A female subject in their 50s. A clinical photograph showing a skin lesion. History notes pesticide exposure and prior skin cancer (patient or family): 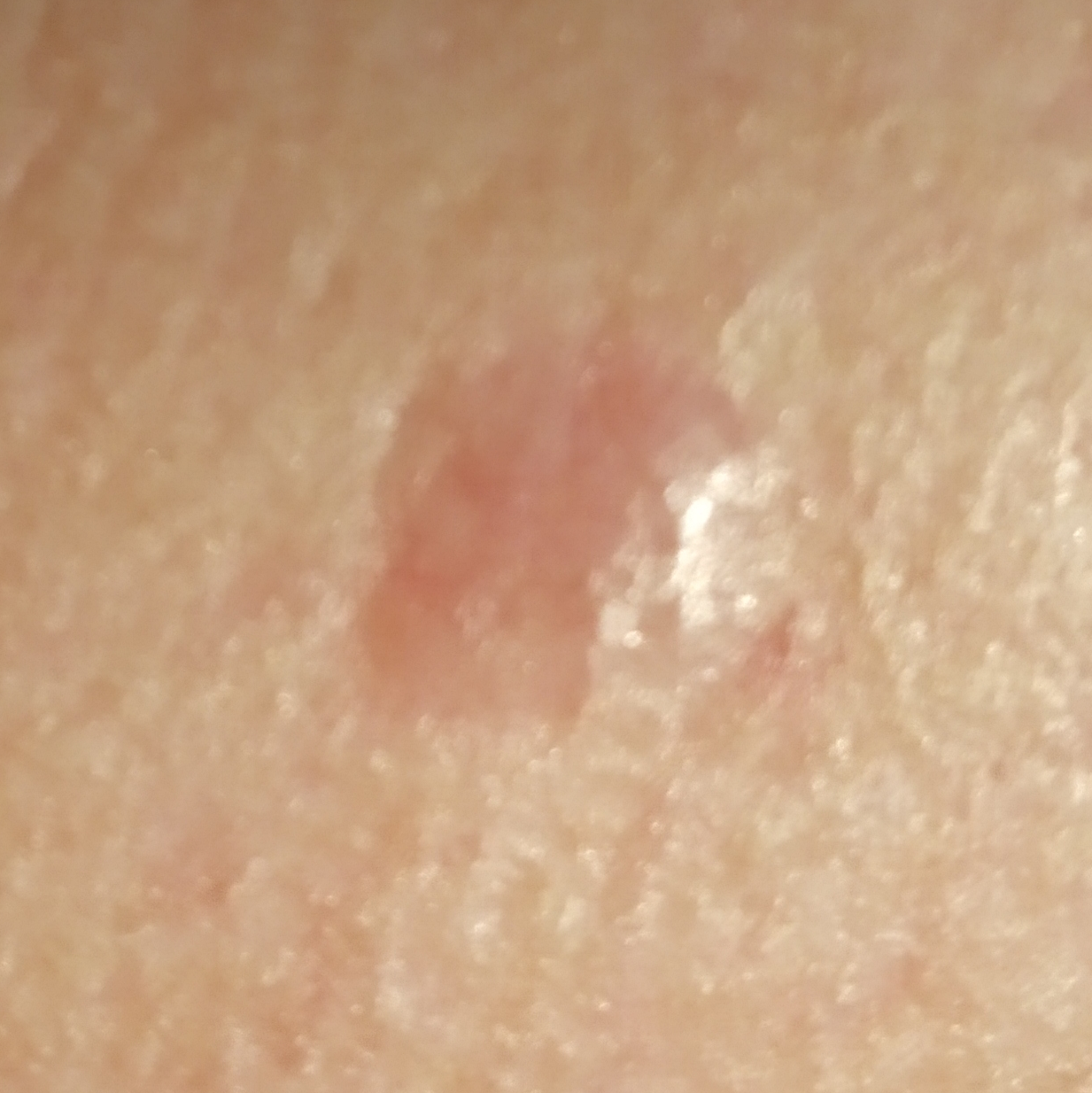The lesion is on the face. The lesion is roughly 9 by 7 mm. Histopathology confirmed a basal cell carcinoma.